The patient considered this a rash. This image was taken at a distance. The condition has been present for less than one week. The lesion involves the arm.
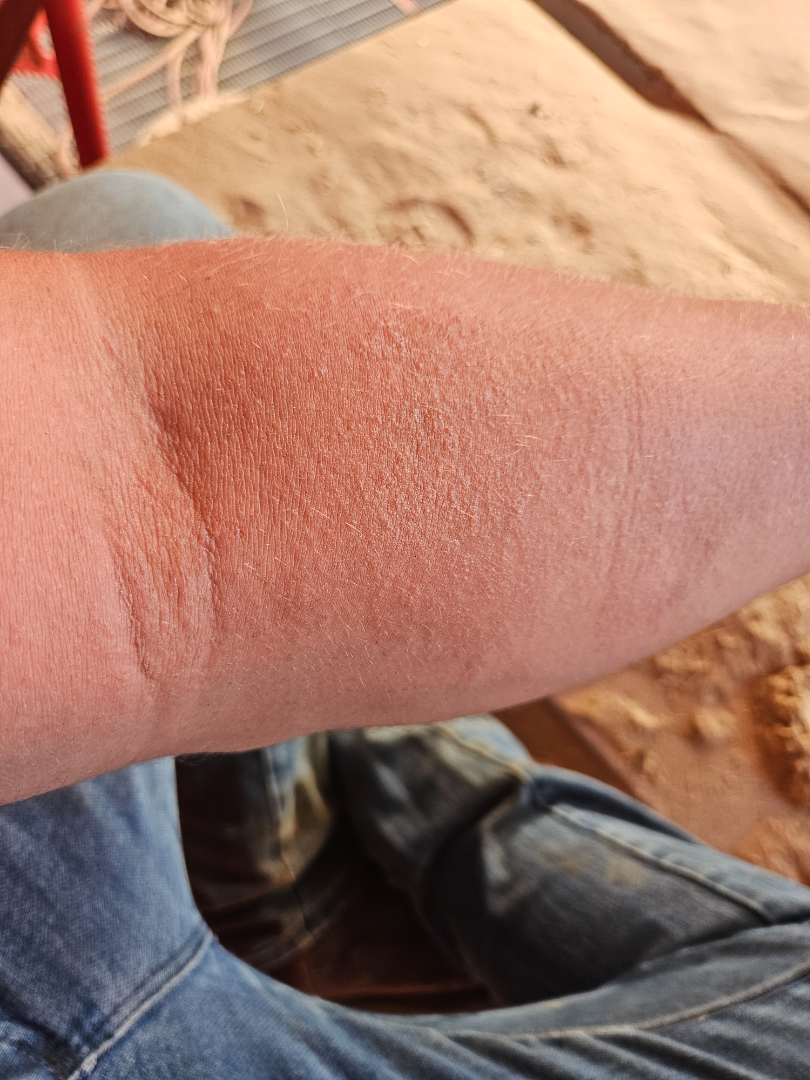diagnostic considerations=three independent reviewers: Allergic Contact Dermatitis, Xerosis and Eczema were each considered, in no particular order; less probable is Sunburn; lower on the differential is Keratosis pilaris.